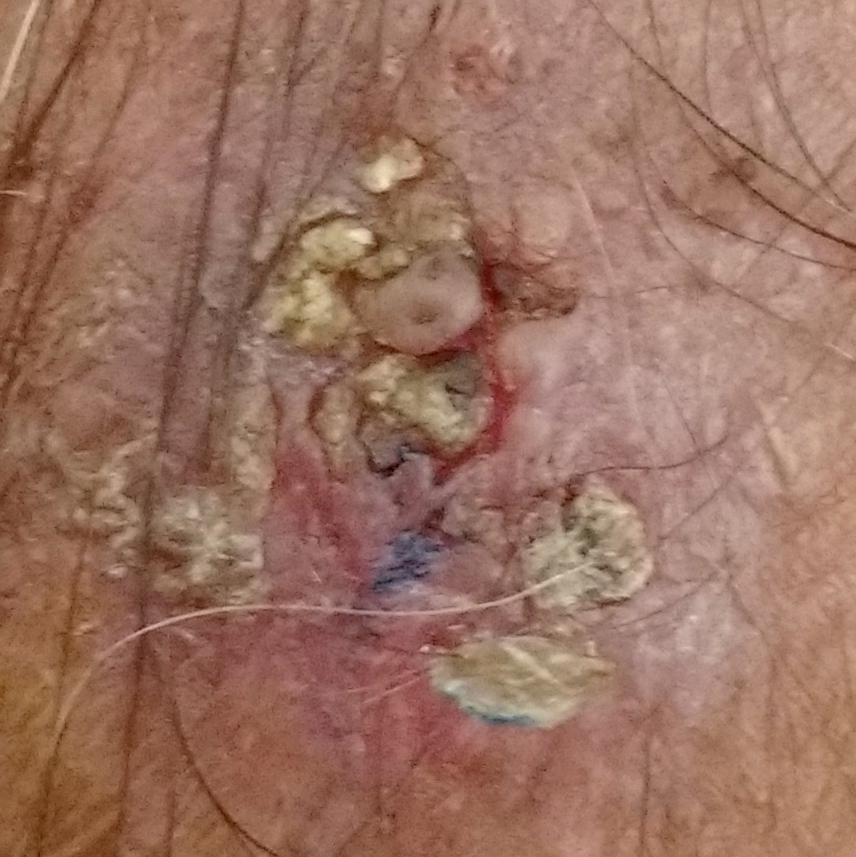Case:
• modality · clinical photo
• FST · IV
• anatomic site · a forearm
• patient-reported symptoms · itching, pain, bleeding / no elevation
• diagnostic label · actinic keratosis (biopsy-proven)